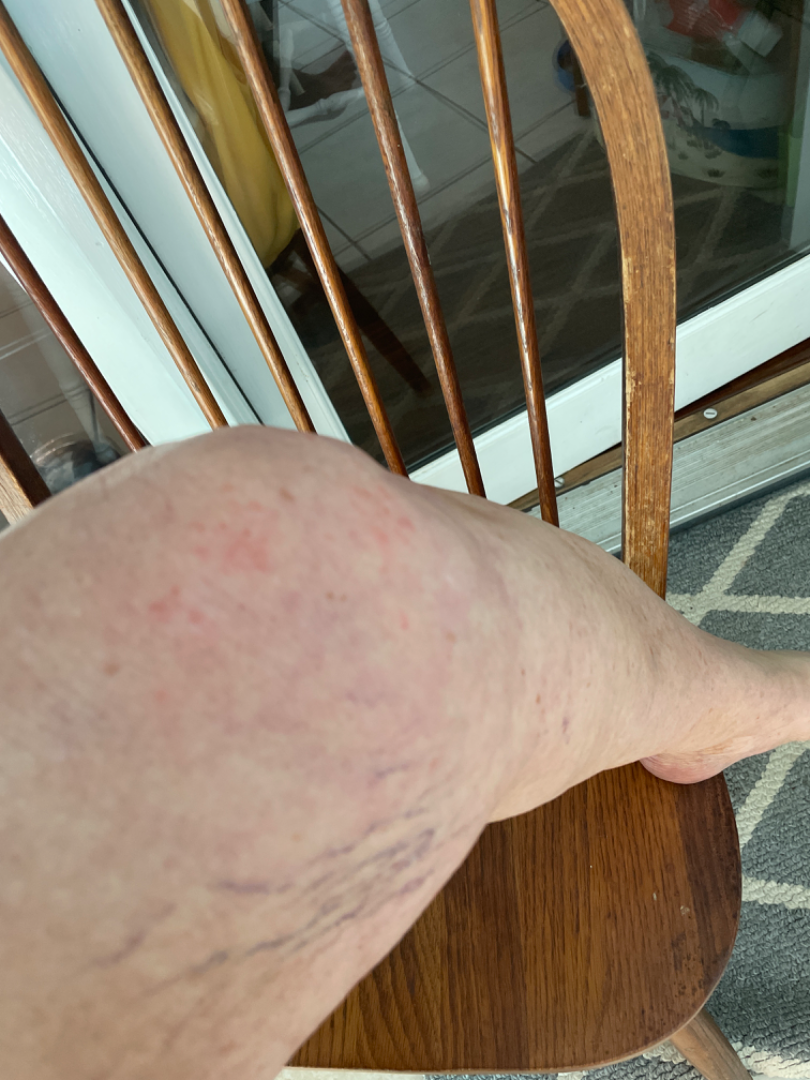affected area: leg
framing: at a distance
contributor: female, age 70–79
dermatologist impression: Psoriasis (considered); Eczema (considered); Dermatitis herpetiformis (considered)